The photograph was taken at a distance. Texture is reported as raised or bumpy. Present for three to twelve months. Located on the leg. Female subject, age 50–59.
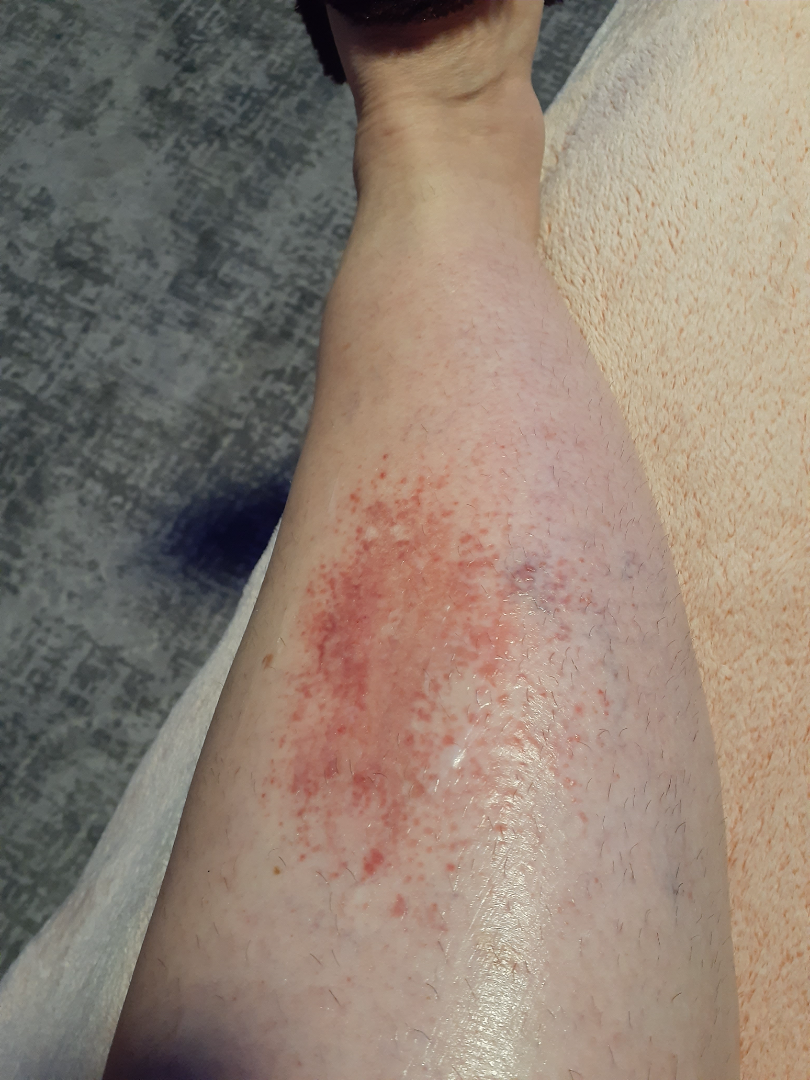Q: What conditions are considered?
A: three independent reviewers: the differential is split between Acute dermatitis, NOS and Stasis Dermatitis; less likely is Eczema; less probable is Burn of skin; a more distant consideration is Allergic Contact Dermatitis; lower on the differential is Amyloidosis of skin